Dermoscopy of a skin lesion.
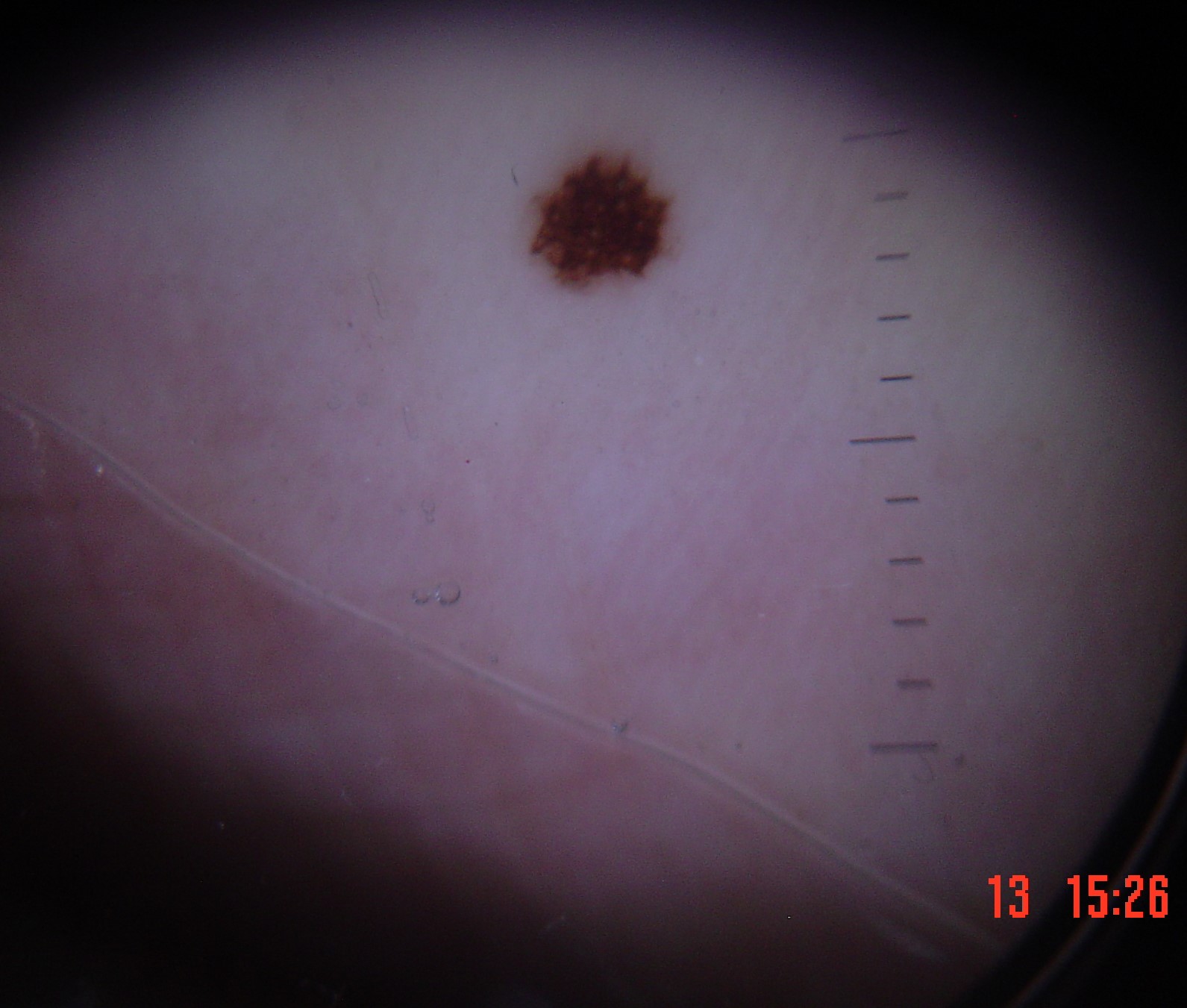Conclusion:
The diagnosis was a benign lesion — an acral dysplastic junctional nevus.